A dermoscopy image of a single skin lesion.
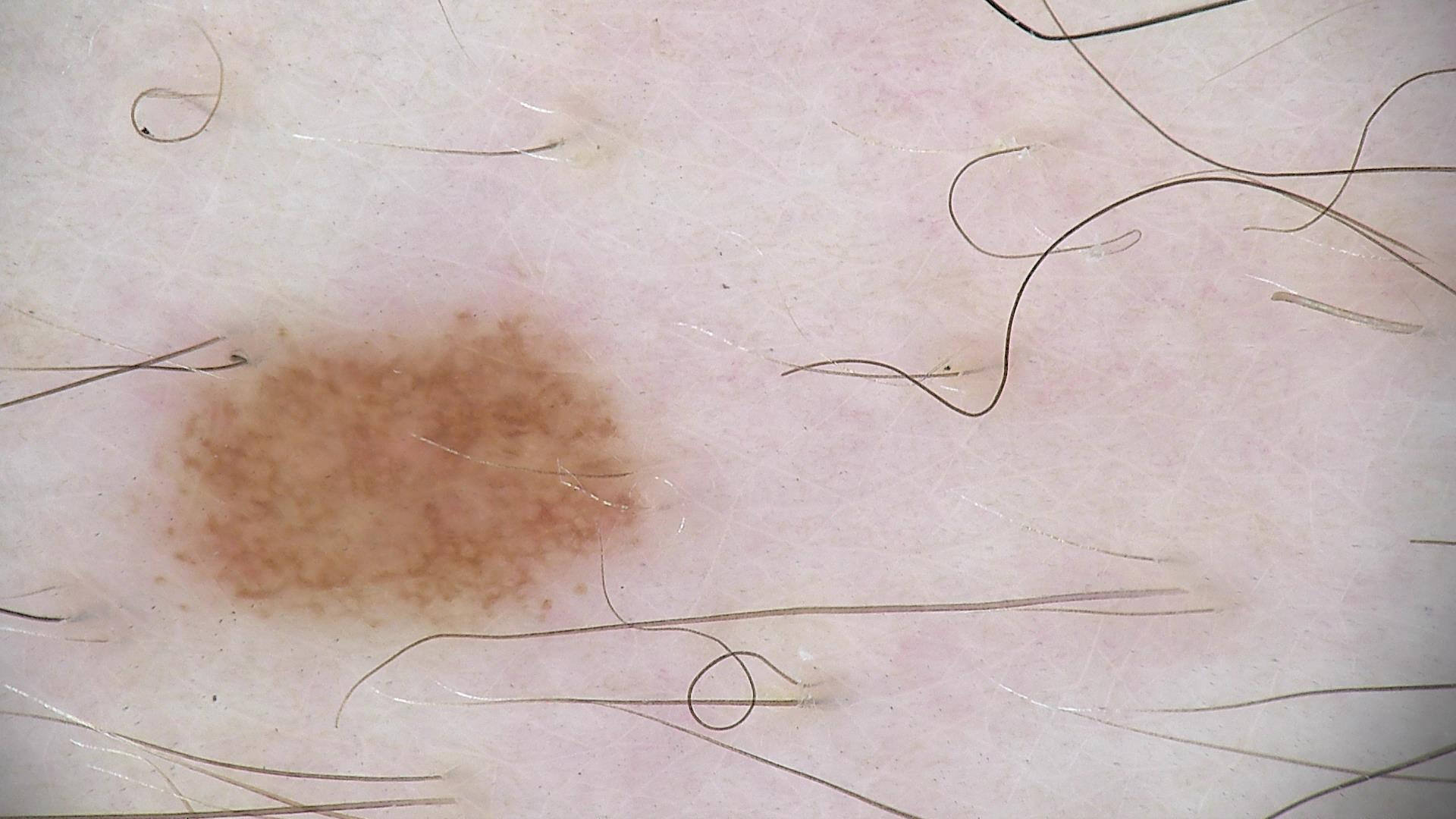  diagnosis:
    name: dysplastic junctional nevus
    code: jd
    malignancy: benign
    super_class: melanocytic
    confirmation: expert consensus